The photograph was taken at an angle.
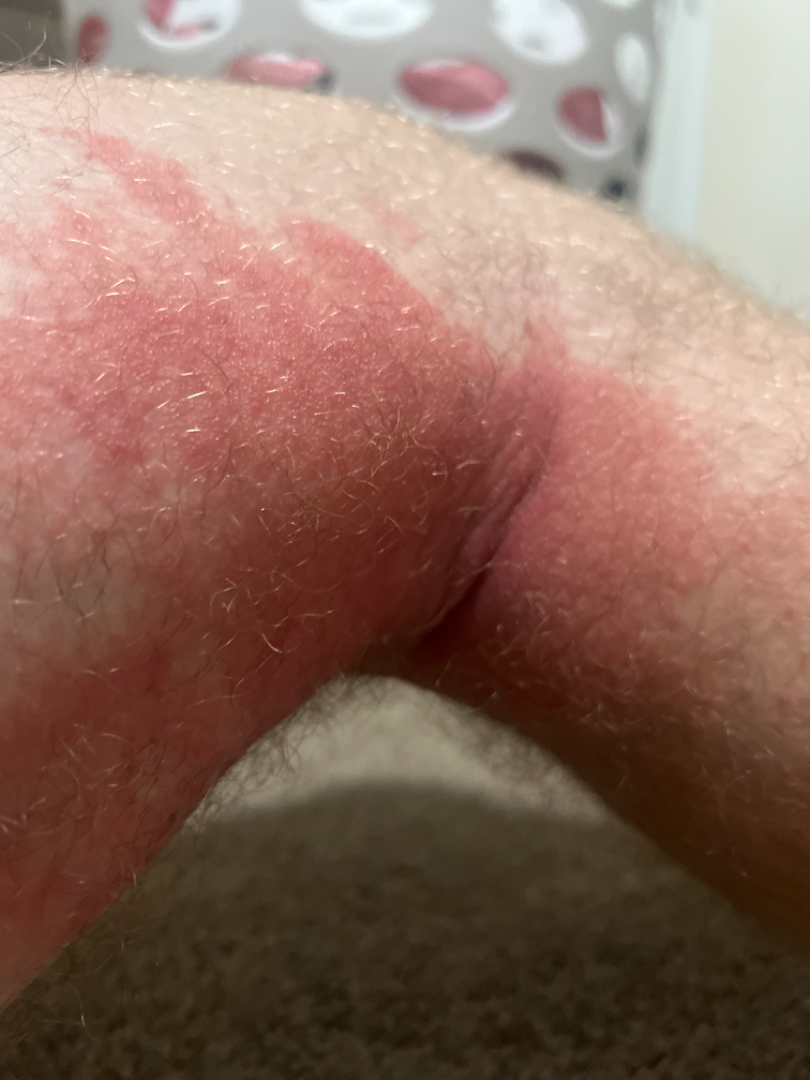<case>
<differential>Allergic Contact Dermatitis</differential>
</case>